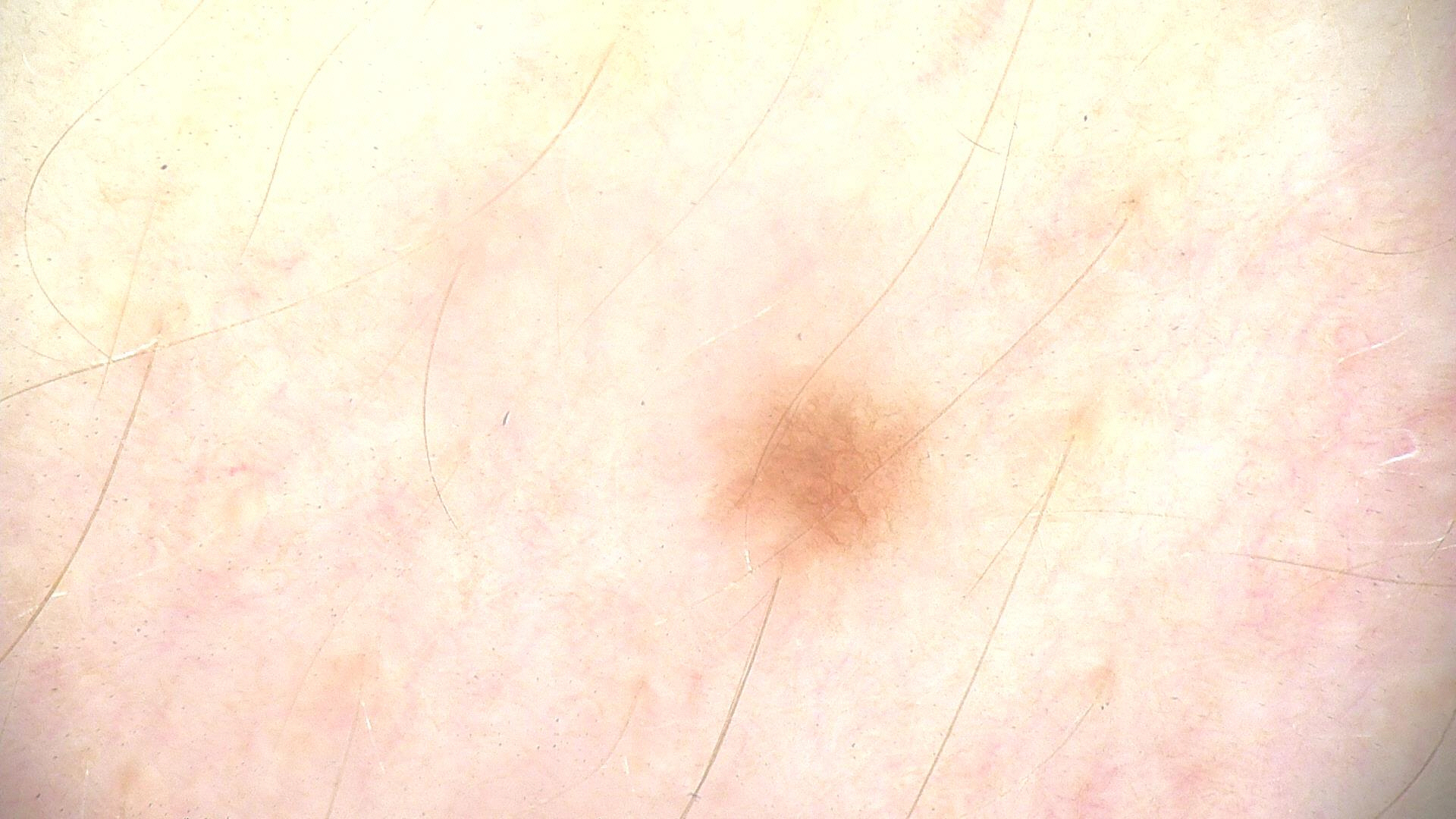modality: dermoscopy
diagnostic label: dysplastic junctional nevus (expert consensus)